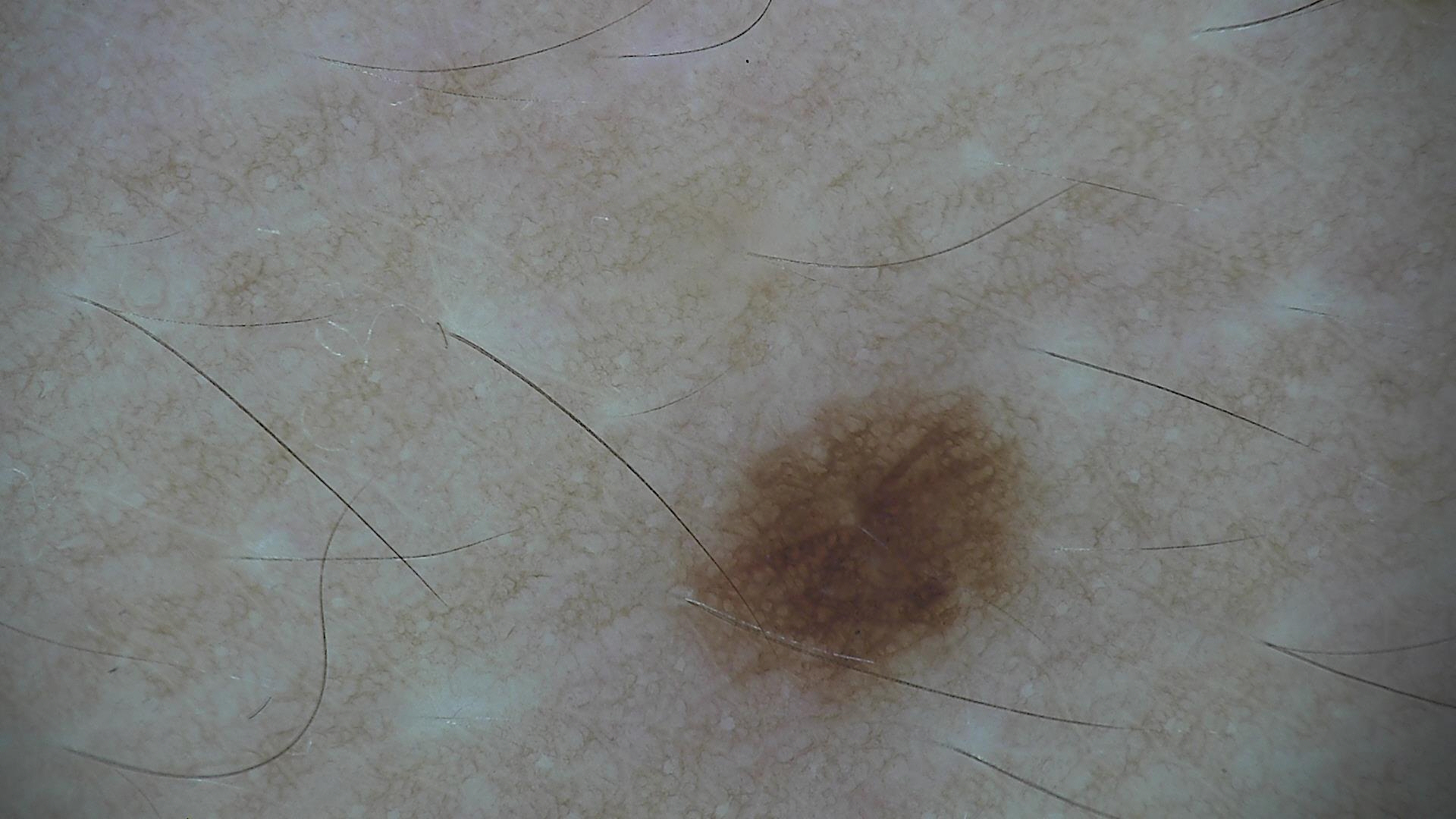Labeled as a dysplastic junctional nevus.